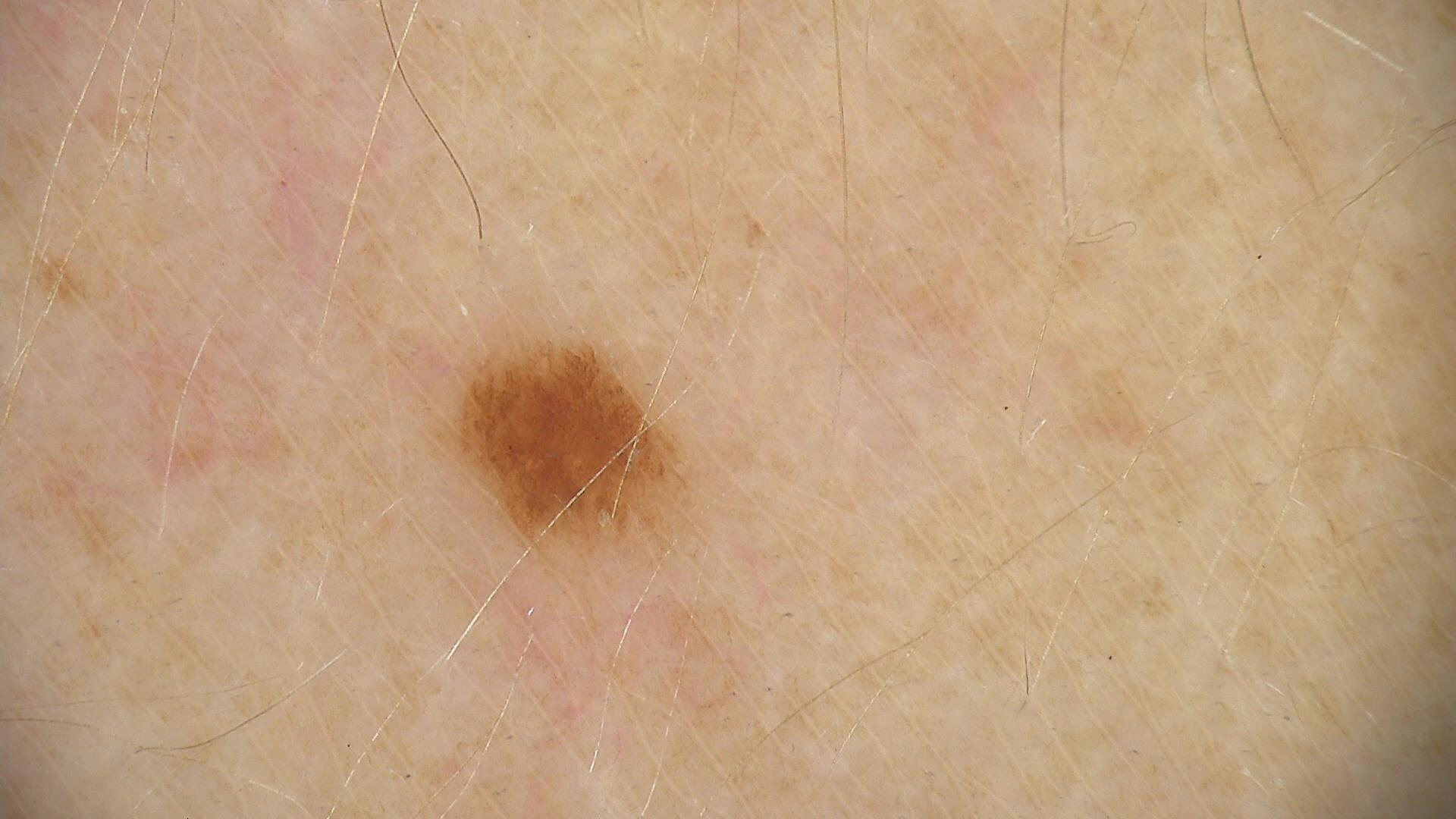A skin lesion imaged with a dermatoscope.
Classified as a benign lesion — a dysplastic junctional nevus.